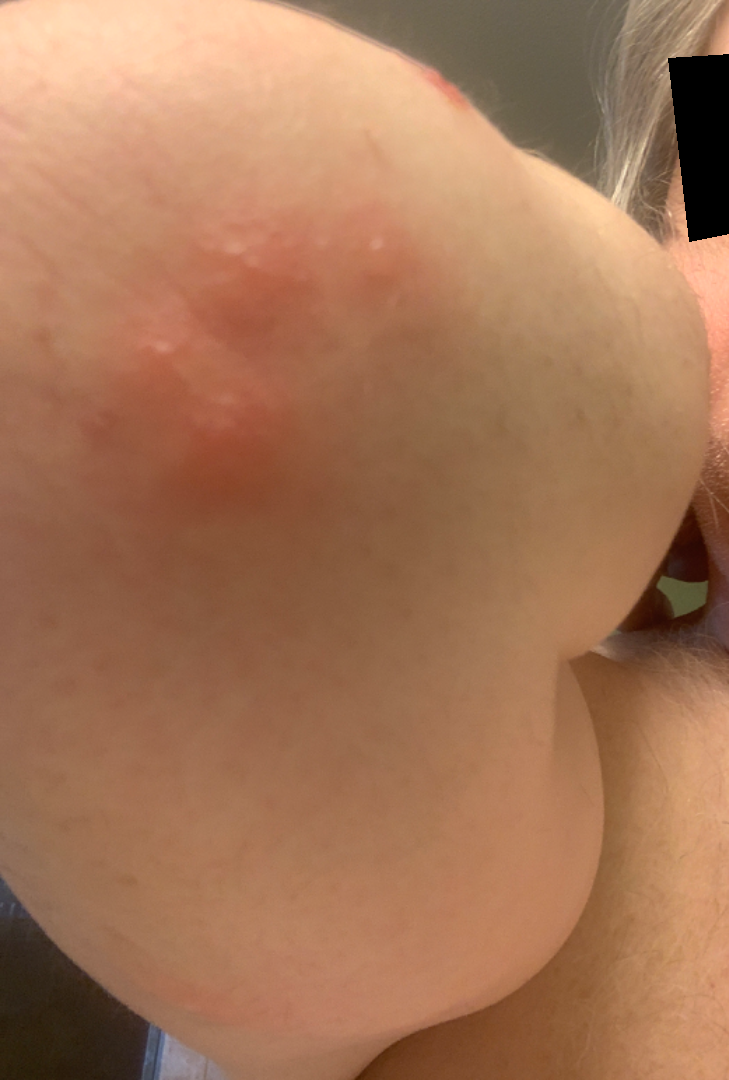assessment=ungradable on photographic review.